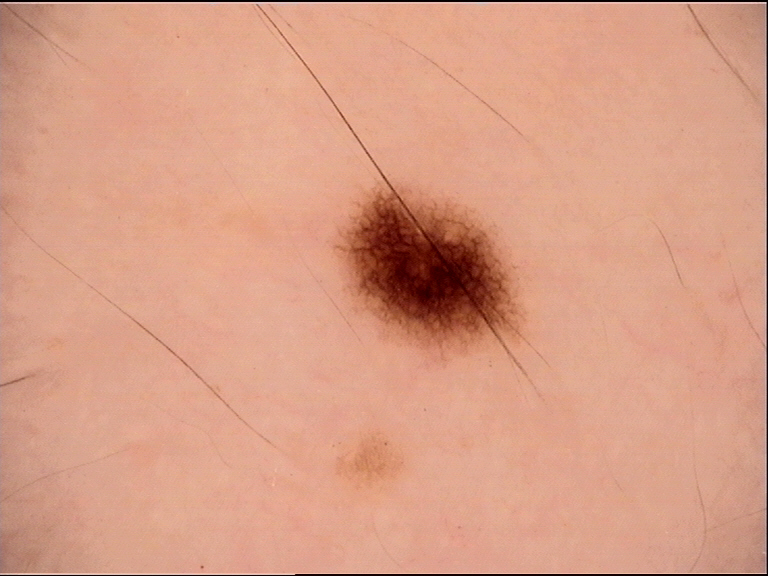Summary:
A dermoscopic image of a skin lesion.
Conclusion:
Labeled as a benign lesion — a dysplastic junctional nevus.